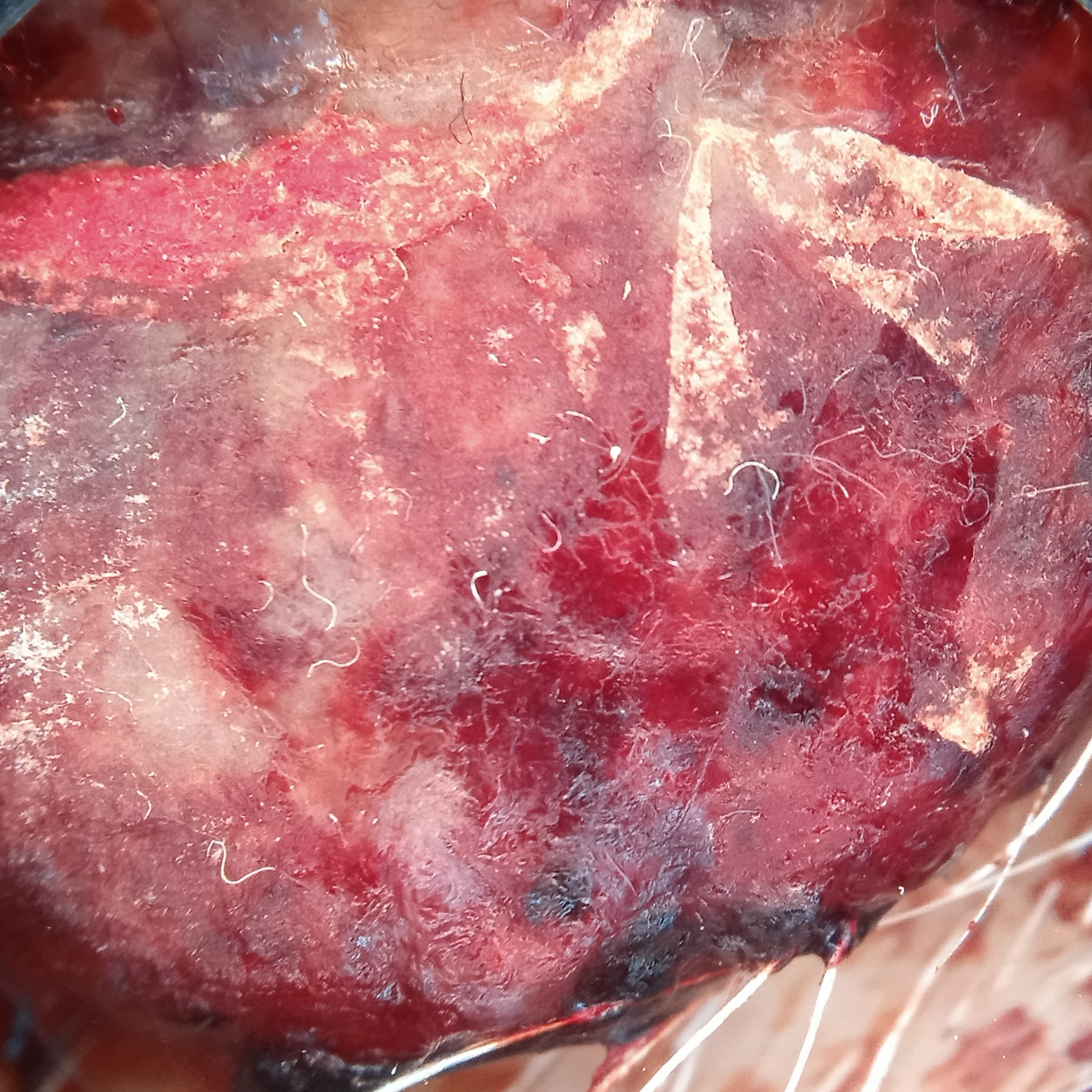The patient describes having few moles overall. Referred for assessment of suspected melanoma. The patient reports a personal history of cancer. A dermoscopy image of a skin lesion. The lesion is on the face. The lesion measures approximately 19.9 mm. Confirmed on histopathology as a melanoma, following excision.